A clinical photo of a skin lesion taken with a smartphone. A patient in their 60s: 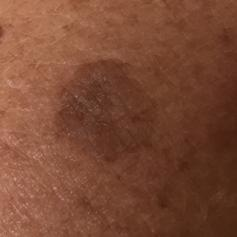| feature | finding |
|---|---|
| site | an arm |
| diagnostic label | seborrheic keratosis (clinical consensus) |